A female patient age 68. By self-report, no personal history of cancer and no sunbed use. Collected as part of a research study, without a referral diagnosis. Few moles overall by the patient's own estimate. The patient says their skin tans without first burning. A dermatoscopic image of a skin lesion:
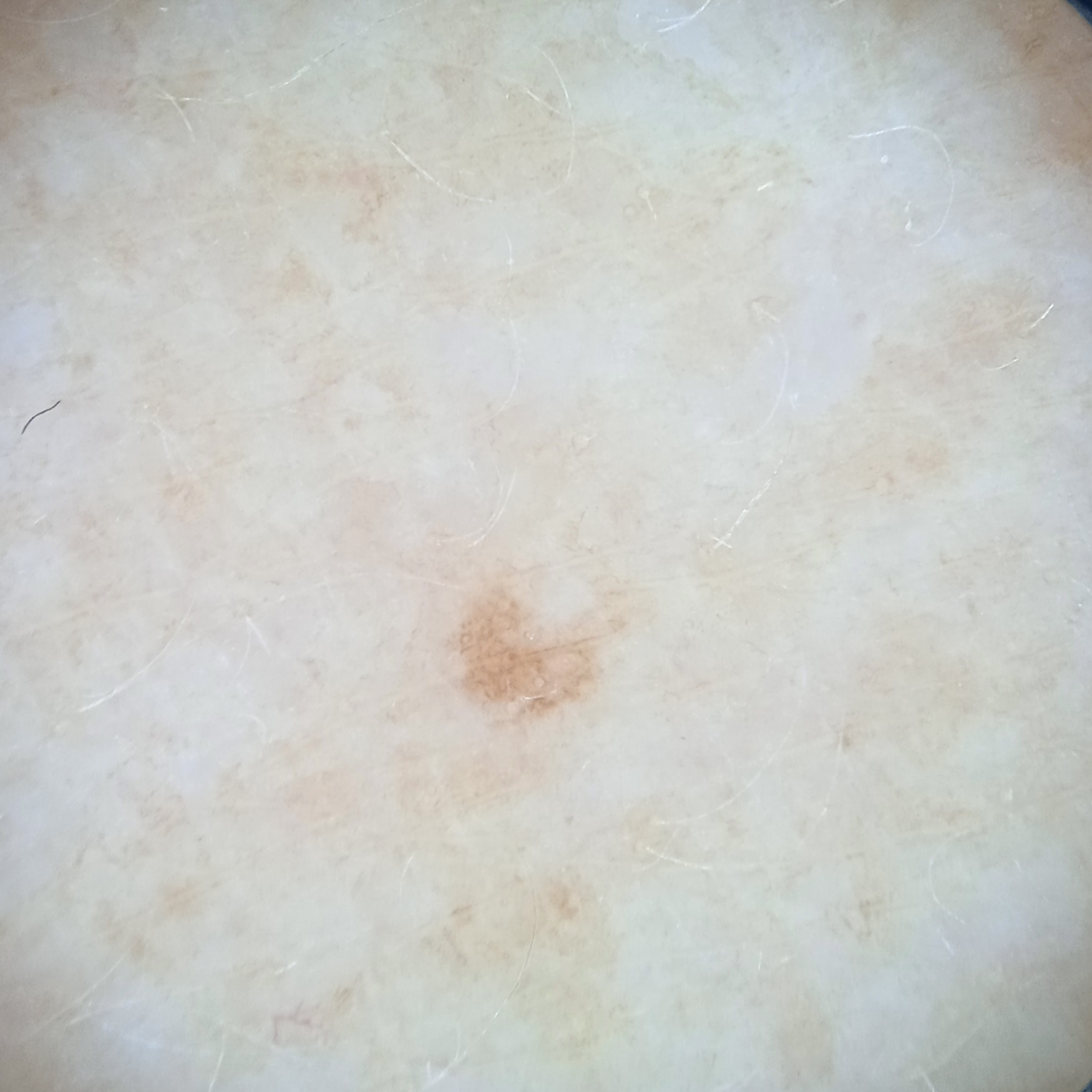Findings:
• site — an arm
• size — 1.7 mm
• assessment — melanocytic nevus (dermatologist consensus)